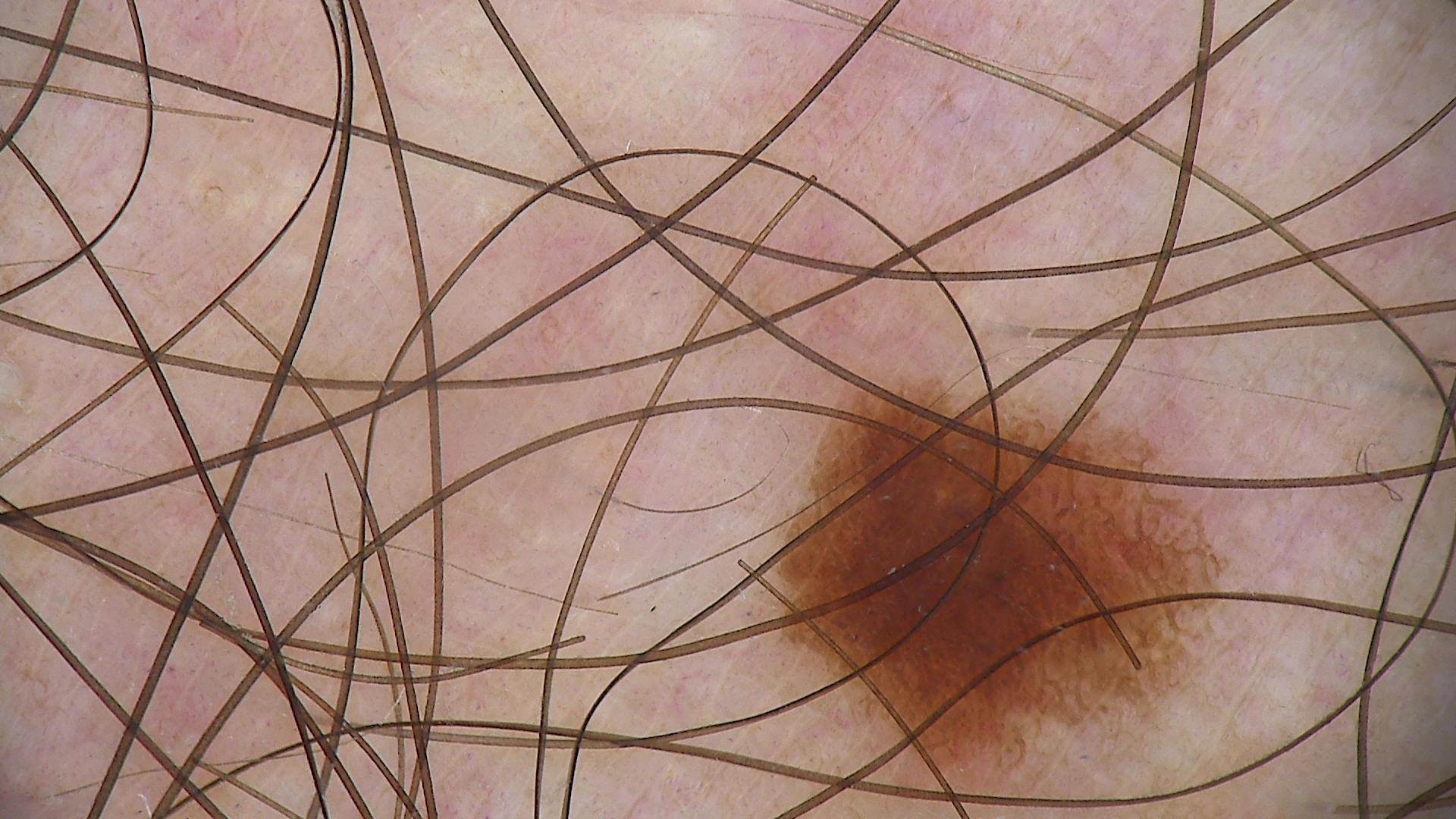Dermoscopy of a skin lesion. Consistent with a junctional nevus.